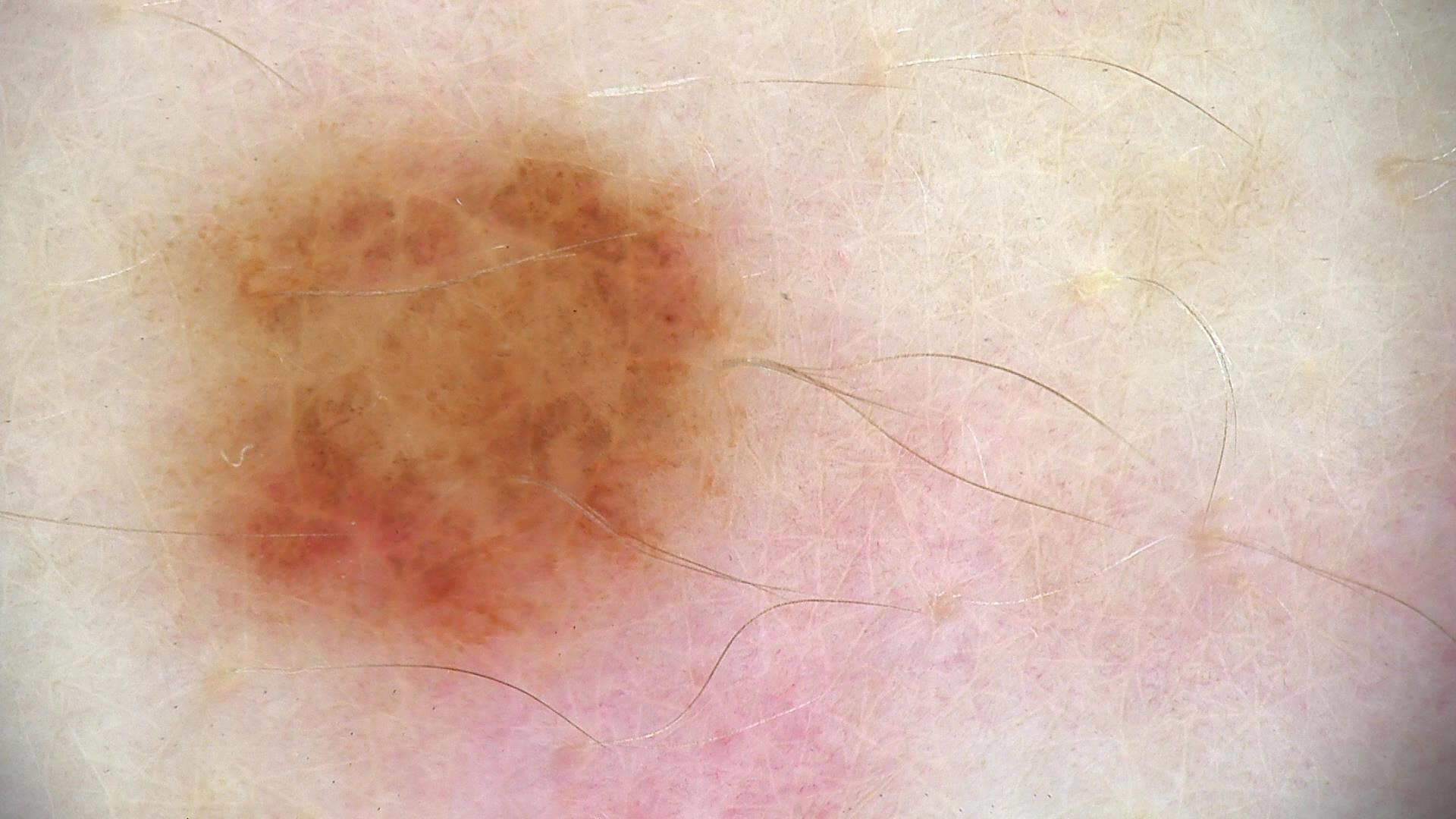| feature | finding |
|---|---|
| assessment | compound nevus (expert consensus) |